A dermoscopic image of a skin lesion:
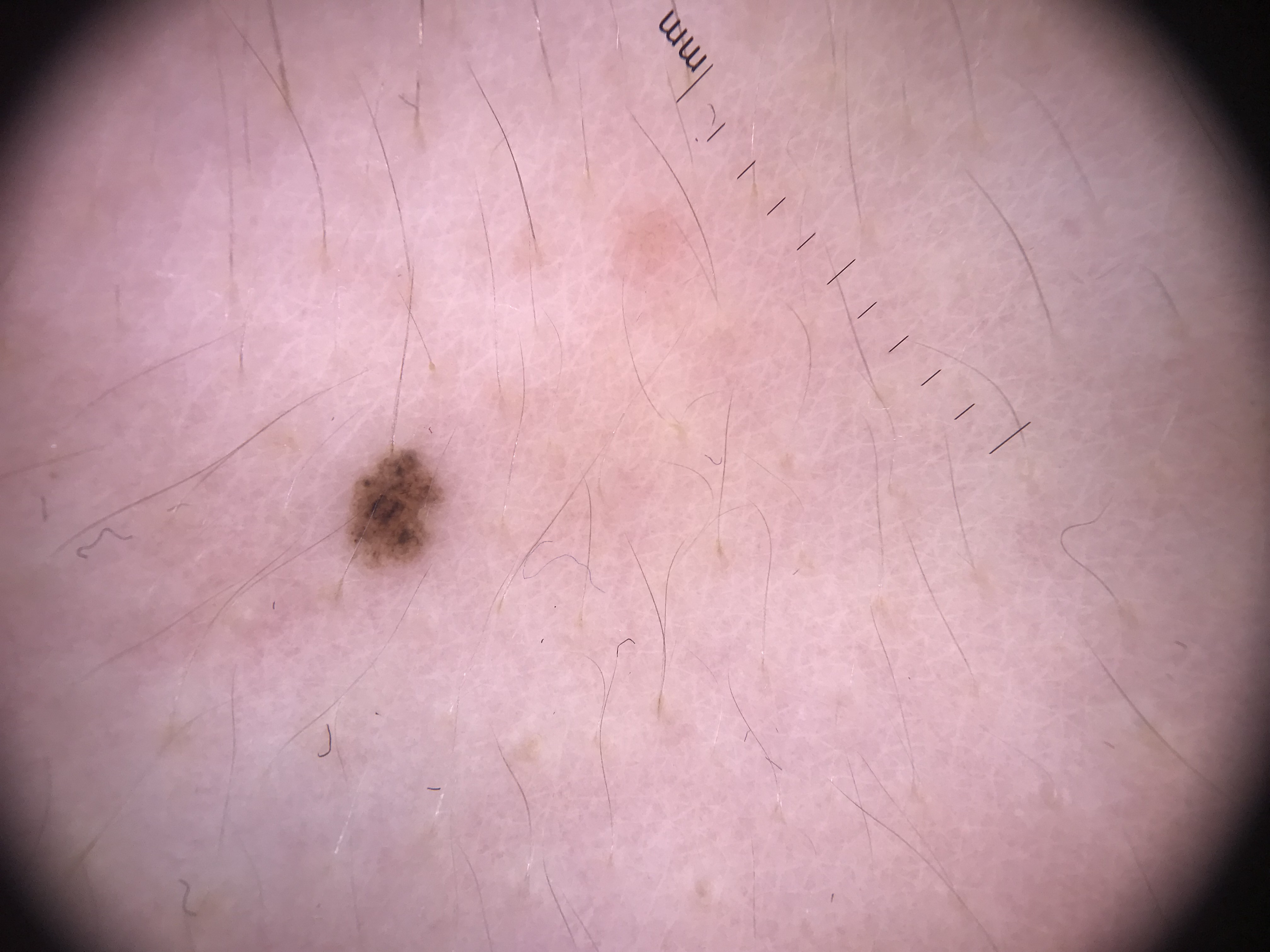category: banal, label: junctional nevus (expert consensus).